A dermoscopy image of a single skin lesion.
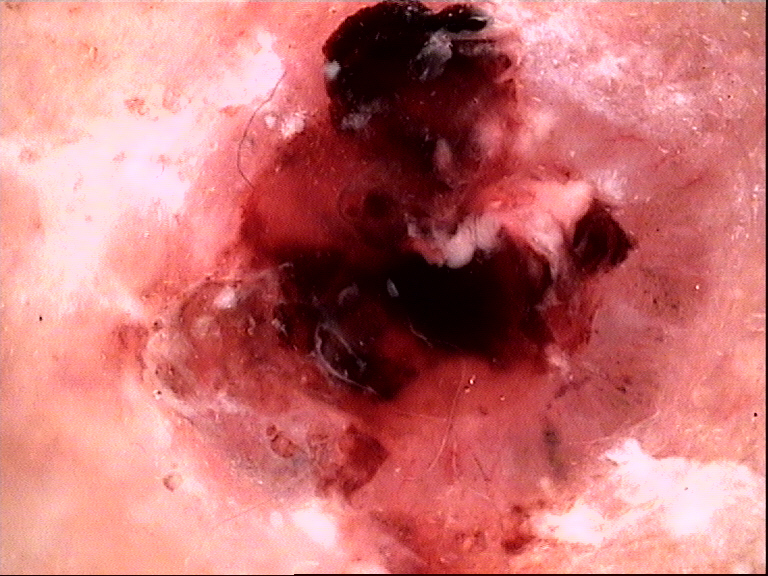Conclusion: Confirmed on histopathology as a keratinocytic lesion — a basal cell carcinoma.